A female patient aged around 85 or older; a wide-field clinical photograph of a skin lesion: 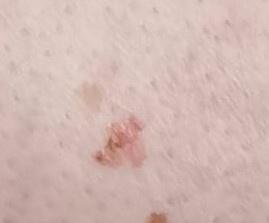Summary: The lesion involves a lower extremity. Diagnosis: Biopsy-confirmed as a melanoma.